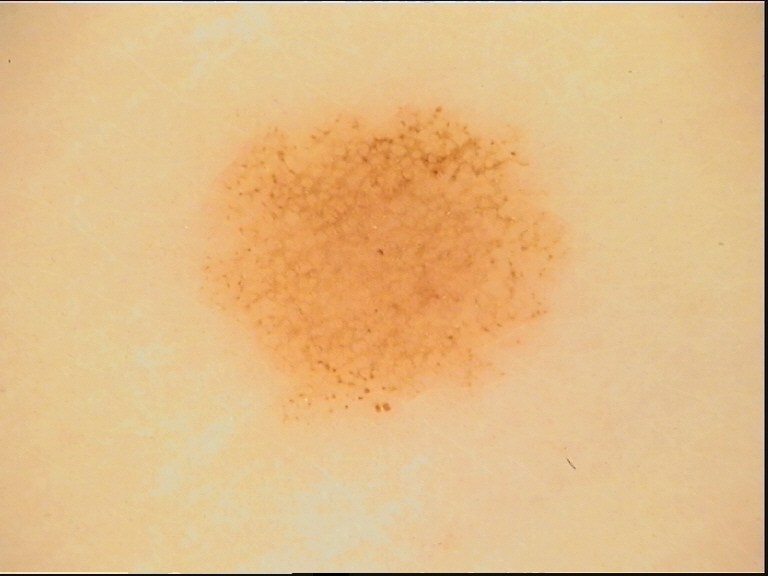Case: A dermoscopic close-up of a skin lesion. Impression: The diagnostic label was a dysplastic junctional nevus.